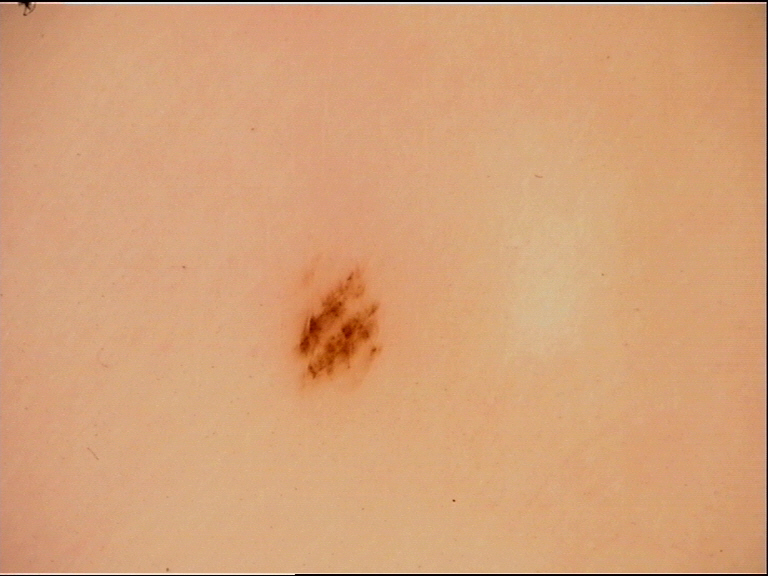The diagnosis was an acral junctional nevus.